Dermoscopy of a skin lesion — 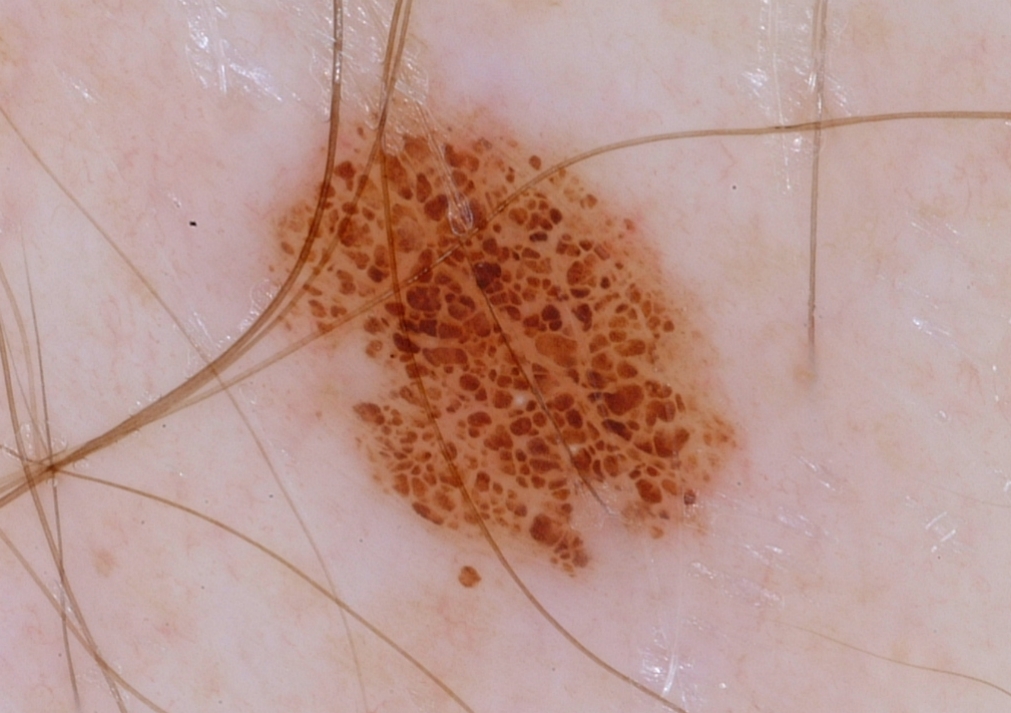Q: Where is the lesion in the image?
A: <bbox>262, 79, 753, 602</bbox>
Q: What dermoscopic features are not present?
A: globules, streaks, negative network, pigment network, and milia-like cysts
Q: What is the diagnosis?
A: a melanocytic nevus